The patient says their skin reddens painfully with sun exposure; the patient reports no immunosuppression and no sunbed use; referred for assessment of suspected basal cell carcinoma; a dermatoscopic image of a skin lesion; a male patient aged 89 — 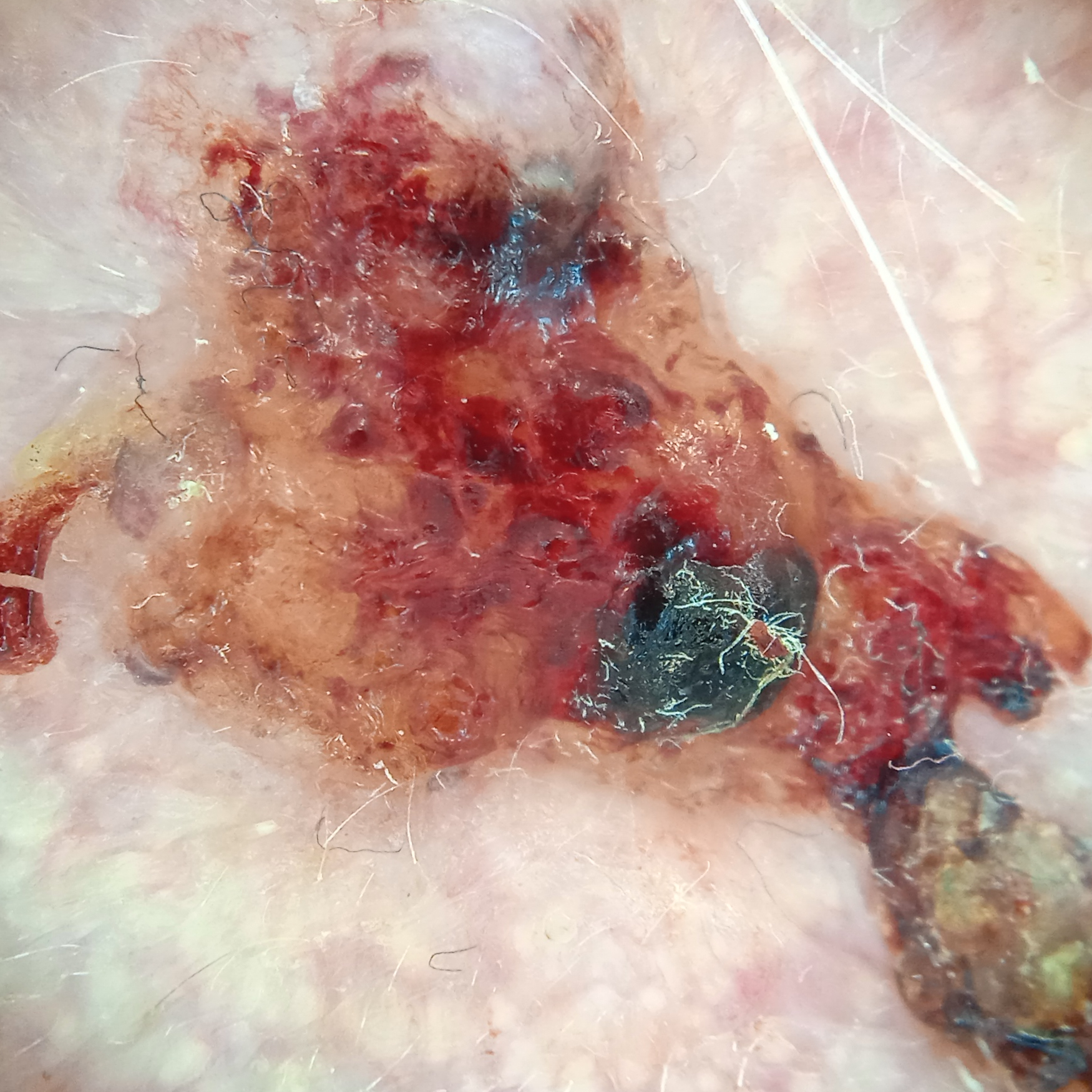Located on the face.
The lesion measures approximately 14.9 mm.
The biopsy diagnosis was a basal cell carcinoma, following excision, with tumor thickness 2 mm.